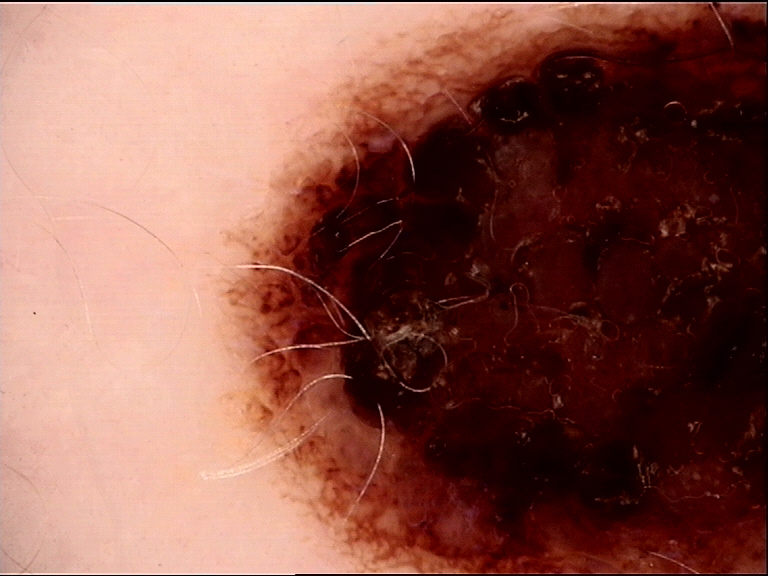Diagnosed as a dysplastic compound nevus.